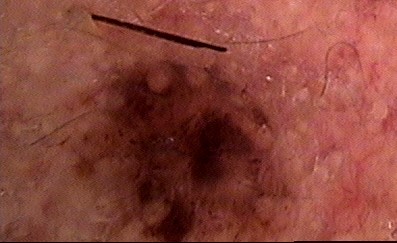Case:
– image type · dermoscopy
– subtype · compound, banal
– class · Miescher nevus (expert consensus)